This image was taken at a distance: 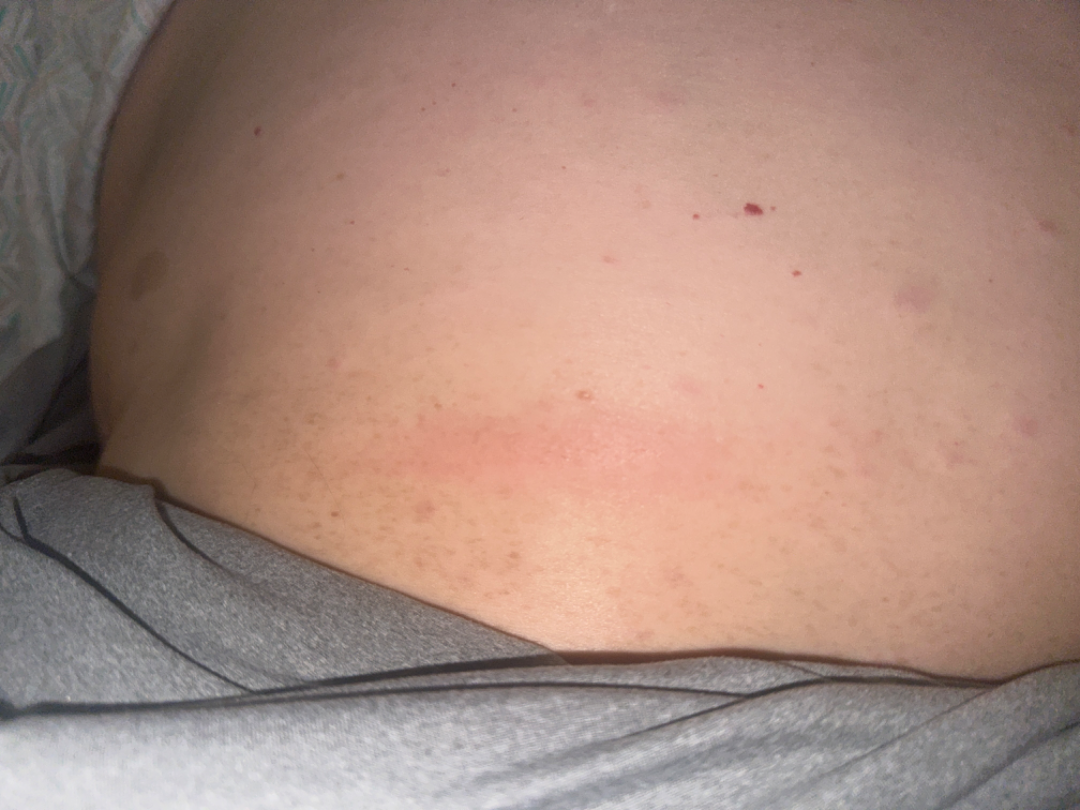Abscess (50%); Cellulitis (50%).